Dermoscopy of a skin lesion.
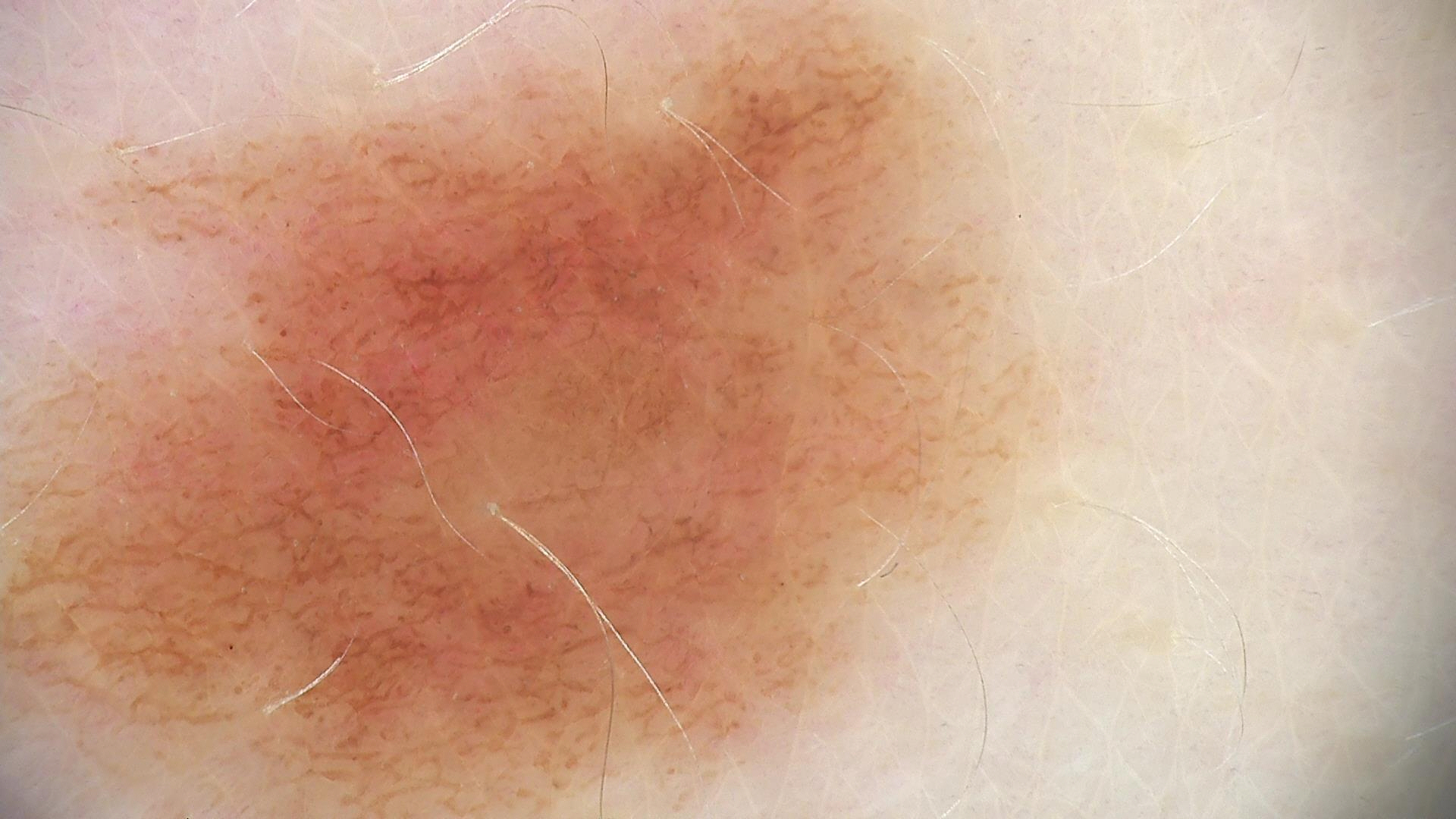Findings:
• label · dysplastic junctional nevus (expert consensus)